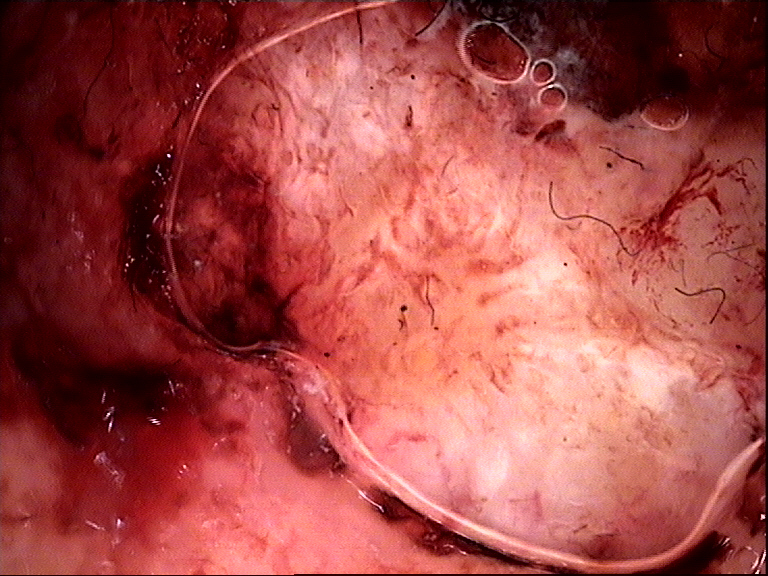{"image": "dermoscopy", "lesion_type": {"main_class": "keratinocytic"}, "diagnosis": {"name": "basal cell carcinoma", "code": "bcc", "malignancy": "malignant", "super_class": "non-melanocytic", "confirmation": "histopathology"}}